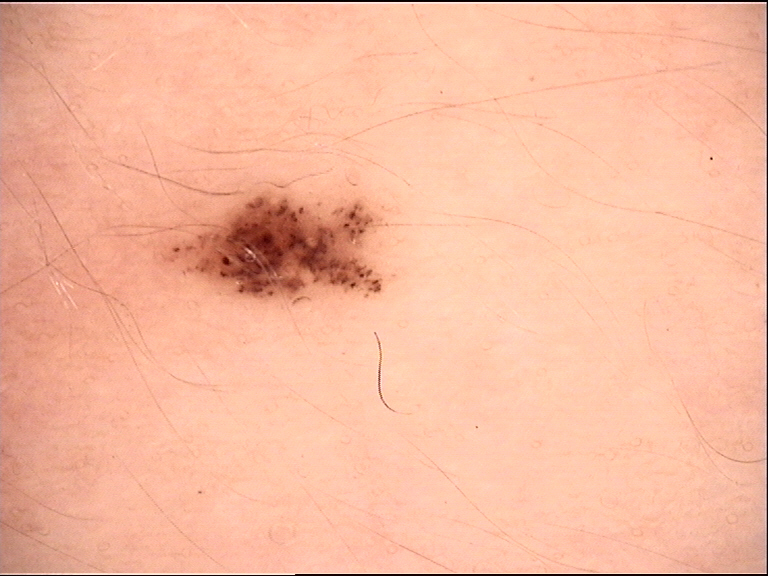| feature | finding |
|---|---|
| image type | dermoscopy |
| label | dysplastic junctional nevus (expert consensus) |